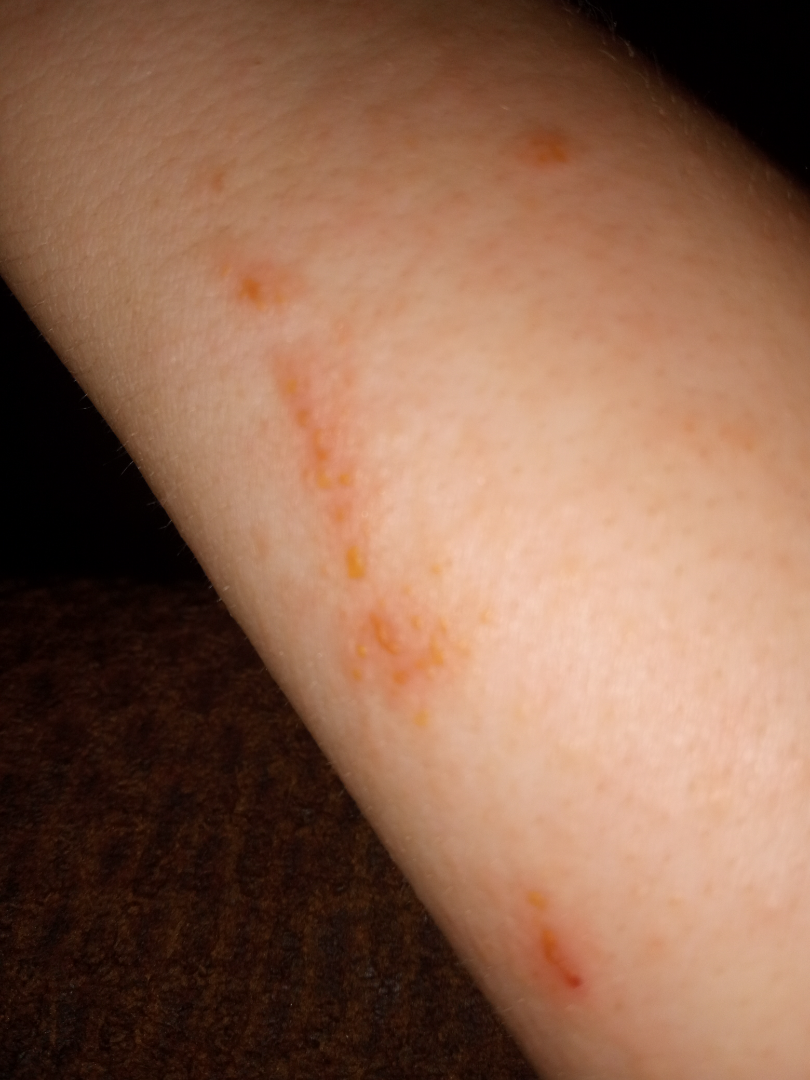The reviewer was unable to grade this case for skin condition.
Located on the arm.
The patient considered this a rash.
The lesion is associated with bothersome appearance, enlargement and itching.
A close-up photograph.
The patient indicates the lesion is raised or bumpy.